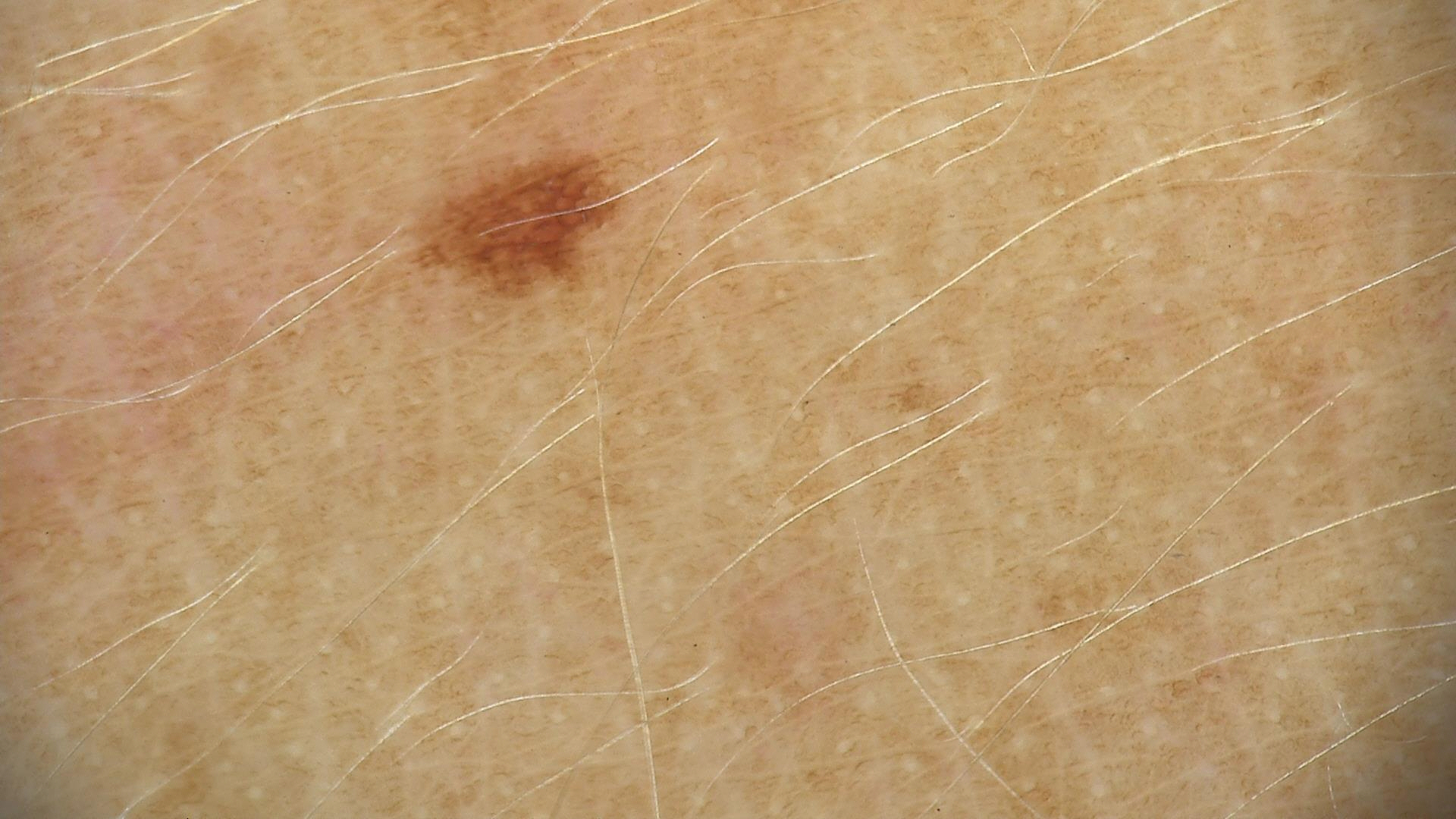Q: What is the imaging modality?
A: dermatoscopy
Q: What is the diagnosis?
A: dysplastic junctional nevus (expert consensus)